A dermoscopy image of a single skin lesion:
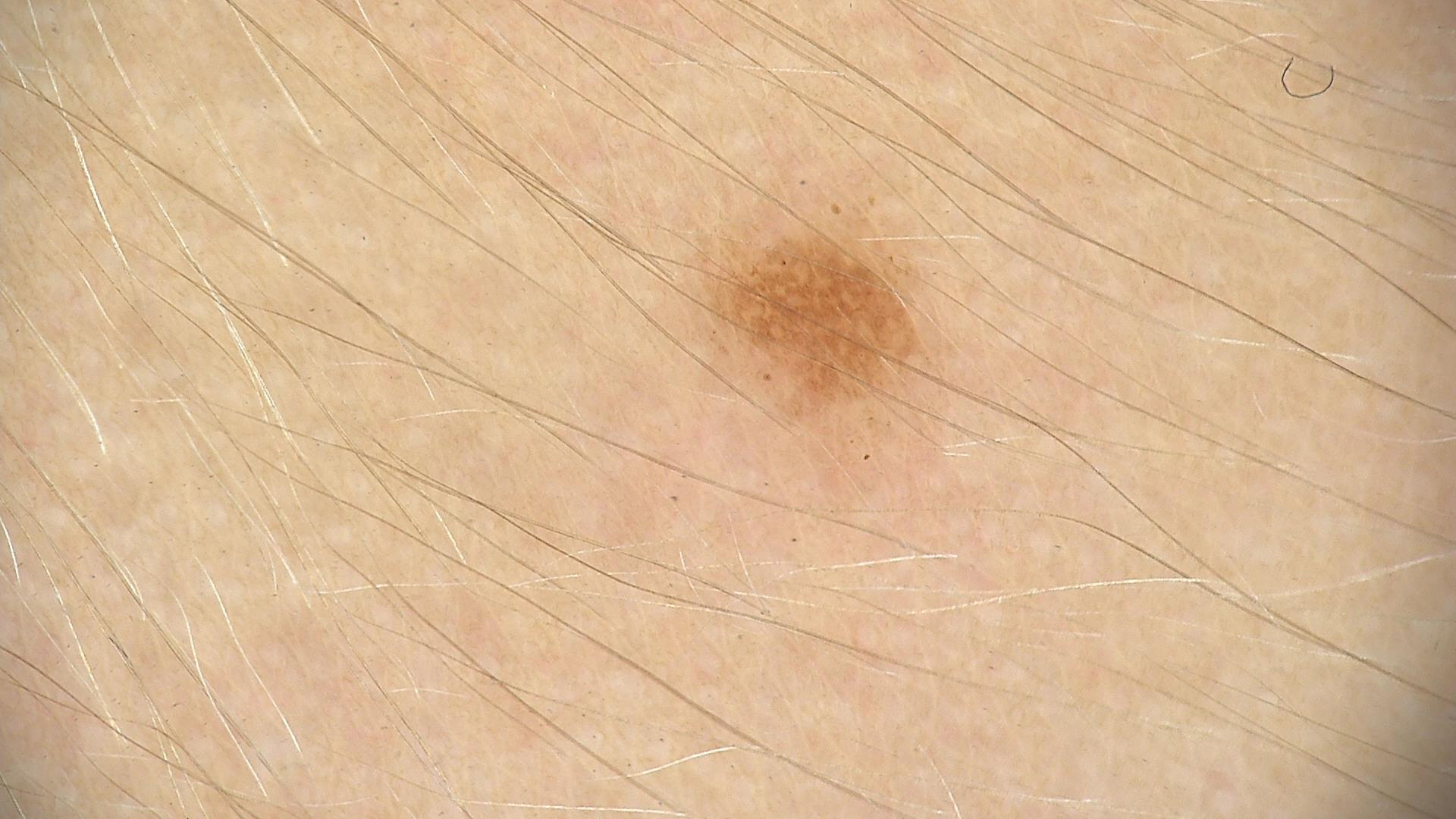The diagnosis was a banal lesion — a junctional nevus.